Close-up view. The lesion involves the front of the torso.
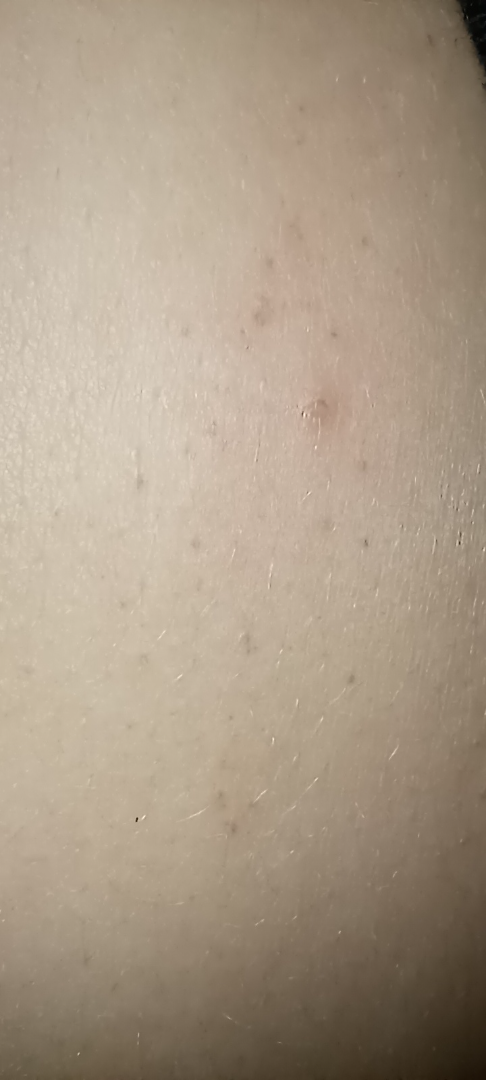assessment: ungradable on photographic review